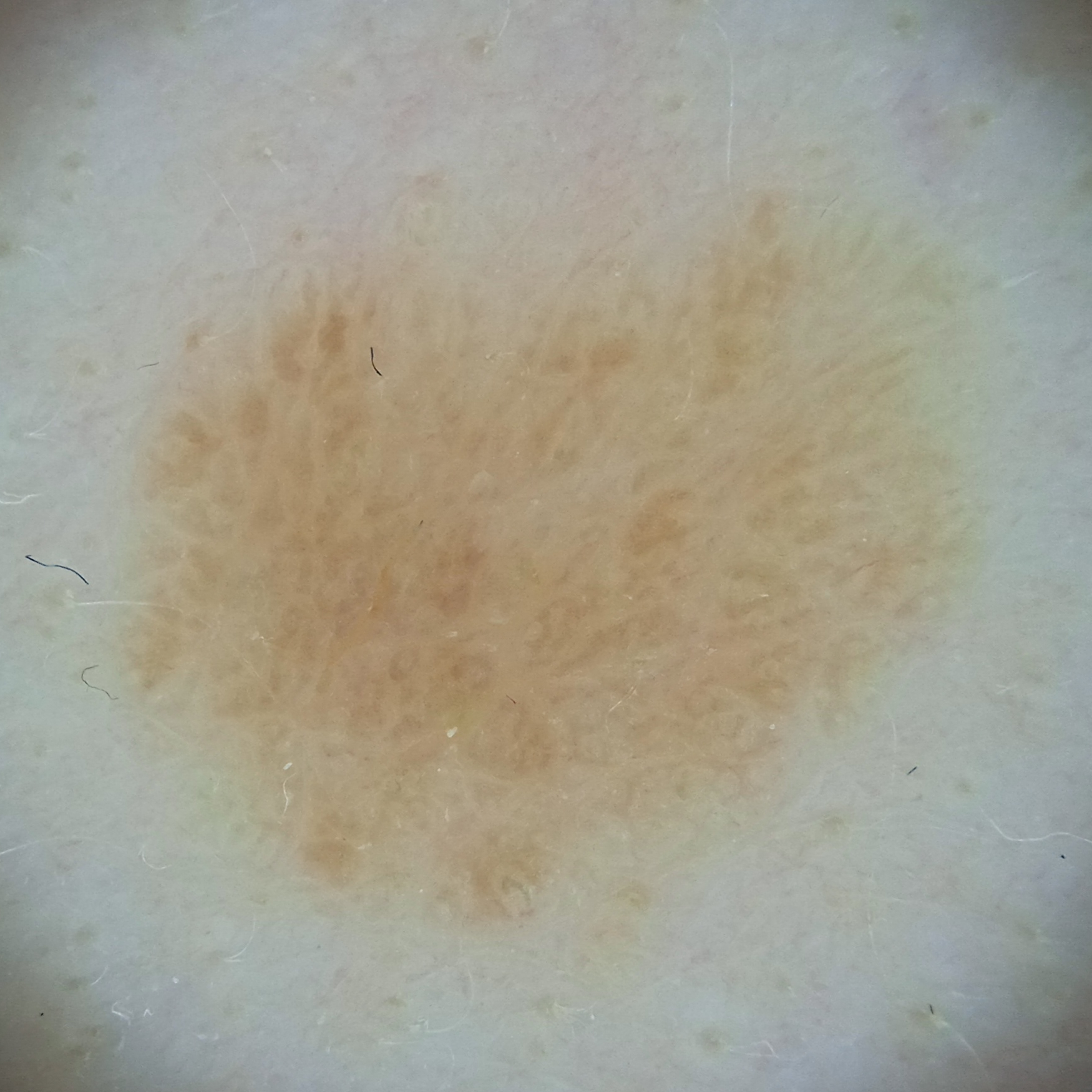referral context = research study (no referral diagnosis); modality = dermoscopic image; sun reaction = skin reddens with sun exposure; nevus count = few melanocytic nevi overall; patient = female, aged 39; diameter = 10.1 mm; diagnostic label = seborrheic keratosis (dermatologist consensus).